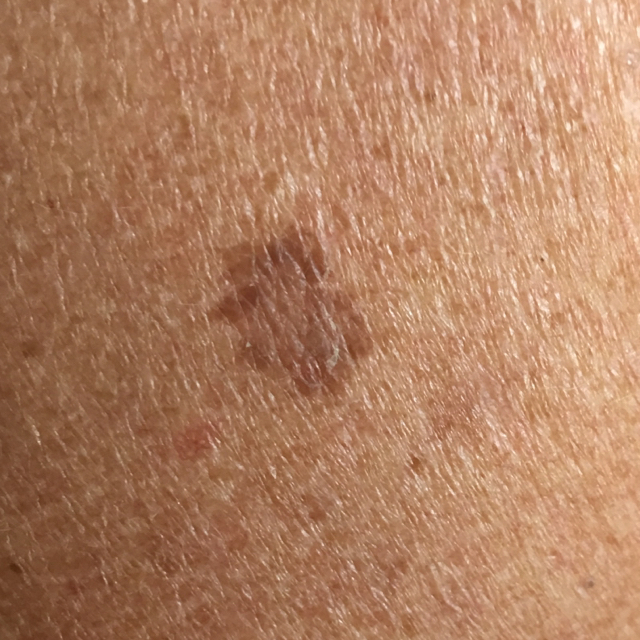{
  "patient": {
    "age": 52
  },
  "image": "smartphone clinical photo",
  "lesion_location": "an arm",
  "symptoms": "none reported",
  "diagnosis": {
    "name": "seborrheic keratosis",
    "code": "SEK",
    "malignancy": "benign",
    "confirmation": "clinical consensus"
  }
}